A smartphone photograph of a skin lesion. The patient was assessed as skin type II. A female patient in their 70s. The chart records no pesticide exposure:
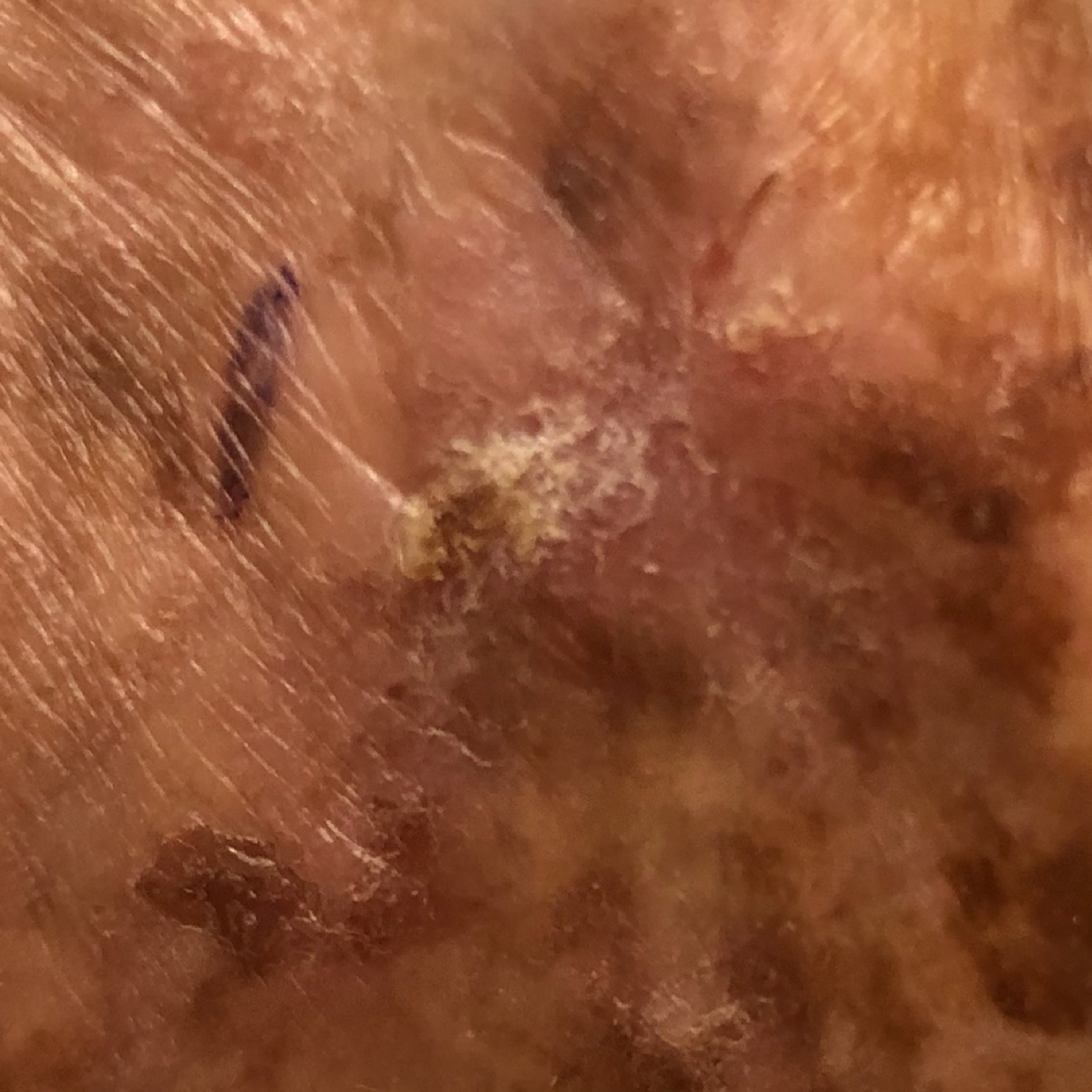| field | value |
|---|---|
| body site | a hand |
| size | 15x10 mm |
| symptoms | change in appearance, elevation / no growth |
| diagnosis | actinic keratosis (biopsy-proven) |